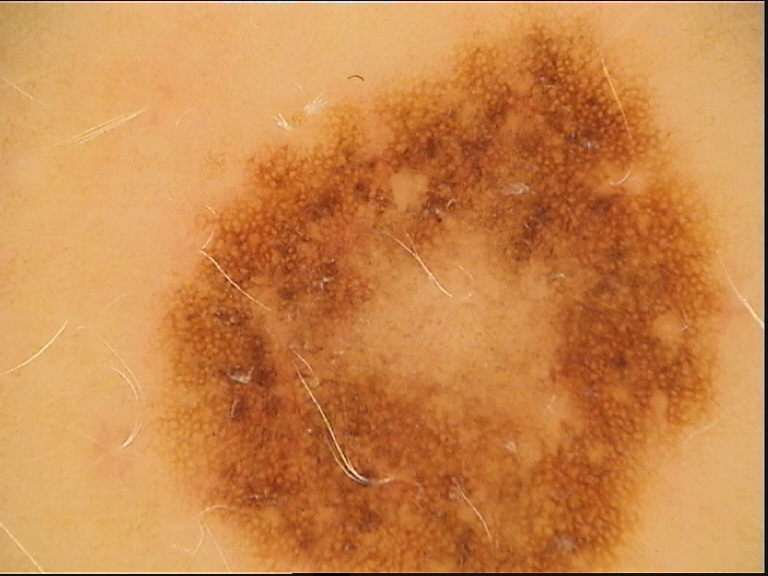{"image": "dermatoscopy", "diagnosis": {"name": "dysplastic junctional nevus", "code": "jd", "malignancy": "benign", "super_class": "melanocytic", "confirmation": "expert consensus"}}